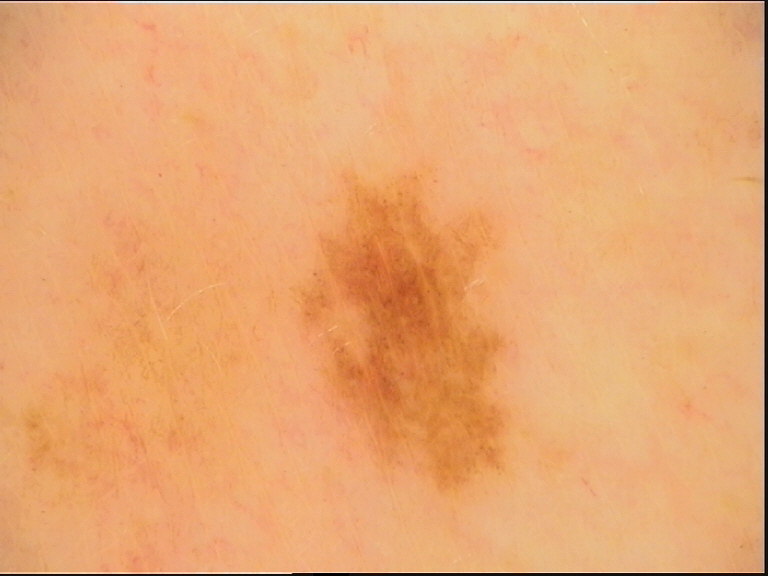label: dysplastic junctional nevus (expert consensus)